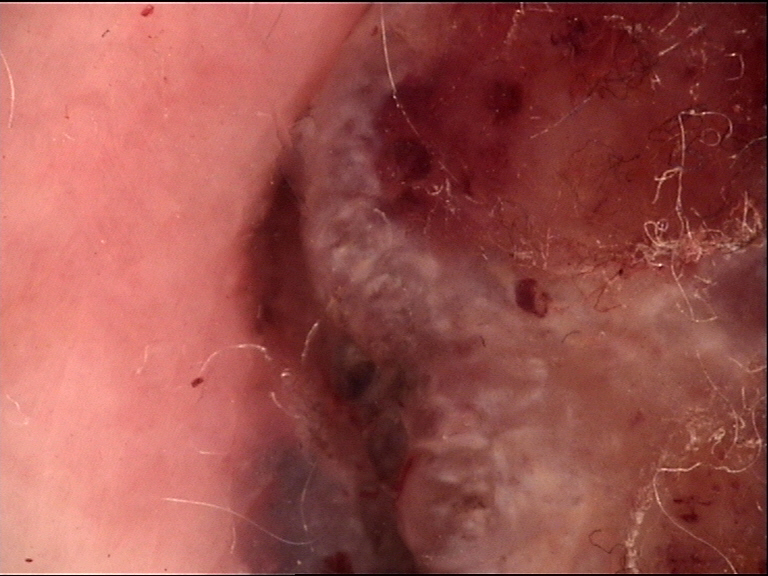Q: What kind of image is this?
A: dermatoscopy
Q: What is the diagnosis?
A: melanoma (biopsy-proven)